The affected area is the top or side of the foot and leg; a close-up photograph; the contributor is 18–29, male: 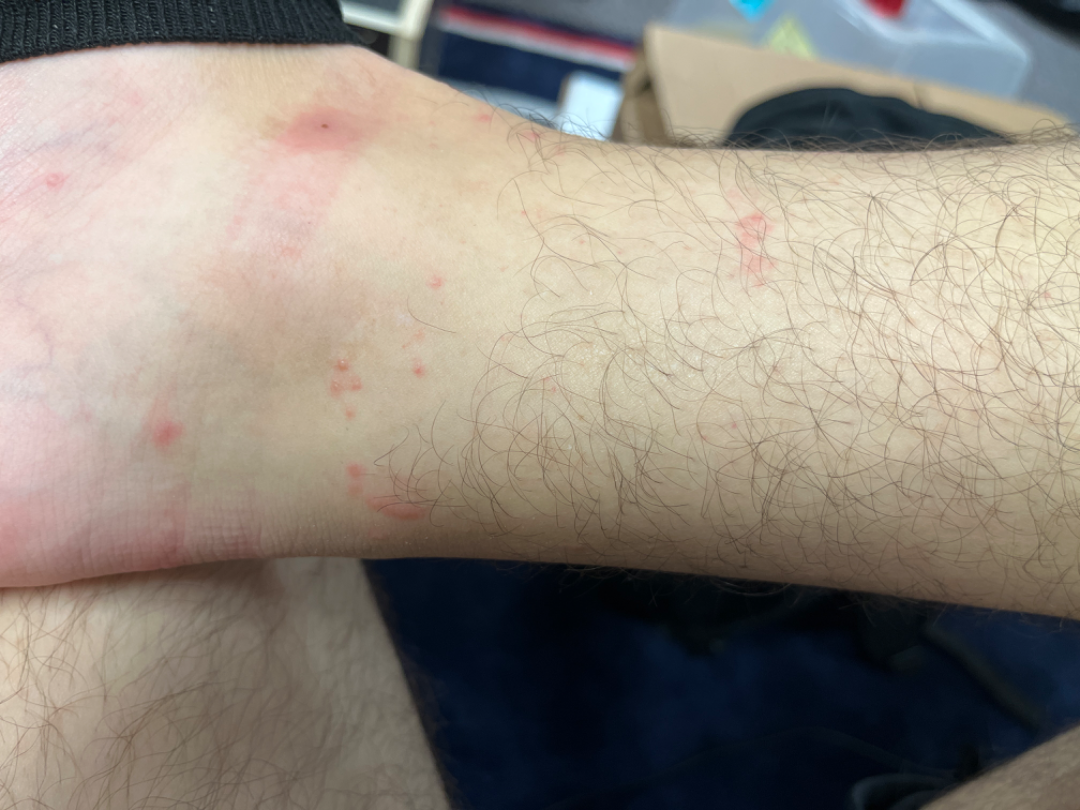The image was not sufficient for the reviewer to characterize the skin condition. The lesion is described as raised or bumpy. The patient reports itching and bleeding. Skin tone: lay graders estimated Monk skin tone scale 2 or 3 (two reviewer pools). The patient described the issue as a rash. No constitutional symptoms were reported. The condition has been present for less than one week.